The sole of the foot is involved. Self-categorized by the patient as skin that appeared healthy to them. The patient reported no systemic symptoms. The photo was captured at an angle. No relevant lesion symptoms reported. Texture is reported as flat. The subject is 30–39, female. The contributor reports the condition has been present for less than one week — 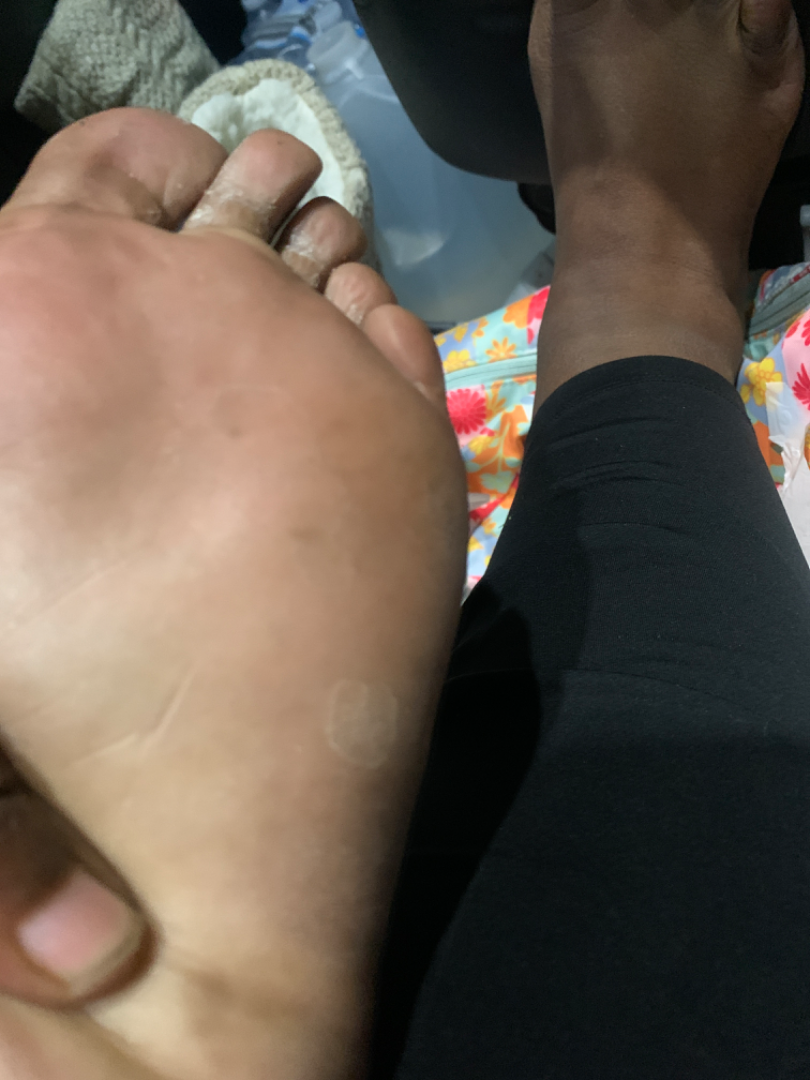Q: Could the case be diagnosed?
A: not assessable